A dermoscopic image of a skin lesion:
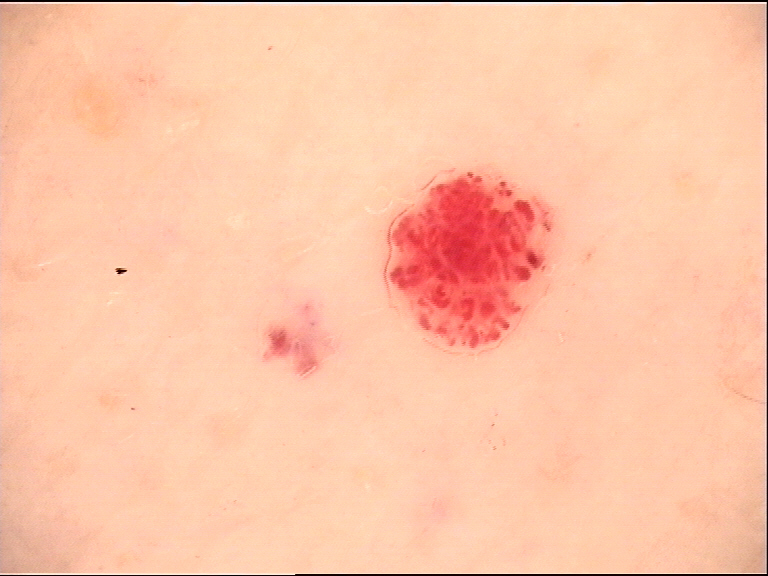subtype: vascular | assessment: hemangioma (expert consensus).